The affected area is the arm. The photo was captured at an angle — 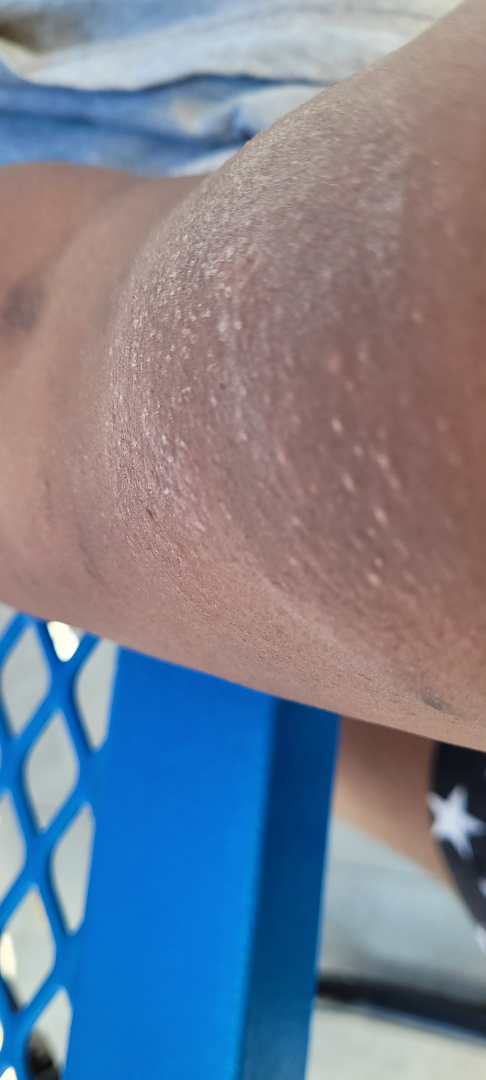Q: What conditions are considered?
A: Chronic dermatitis, NOS and Eczema were considered with similar weight; less probable is Photodermatitis; less likely is Sunburn; a more distant consideration is Lichen nitidus; lower on the differential is Lichen Simplex Chronicus; a remote consideration is Allergic Contact Dermatitis